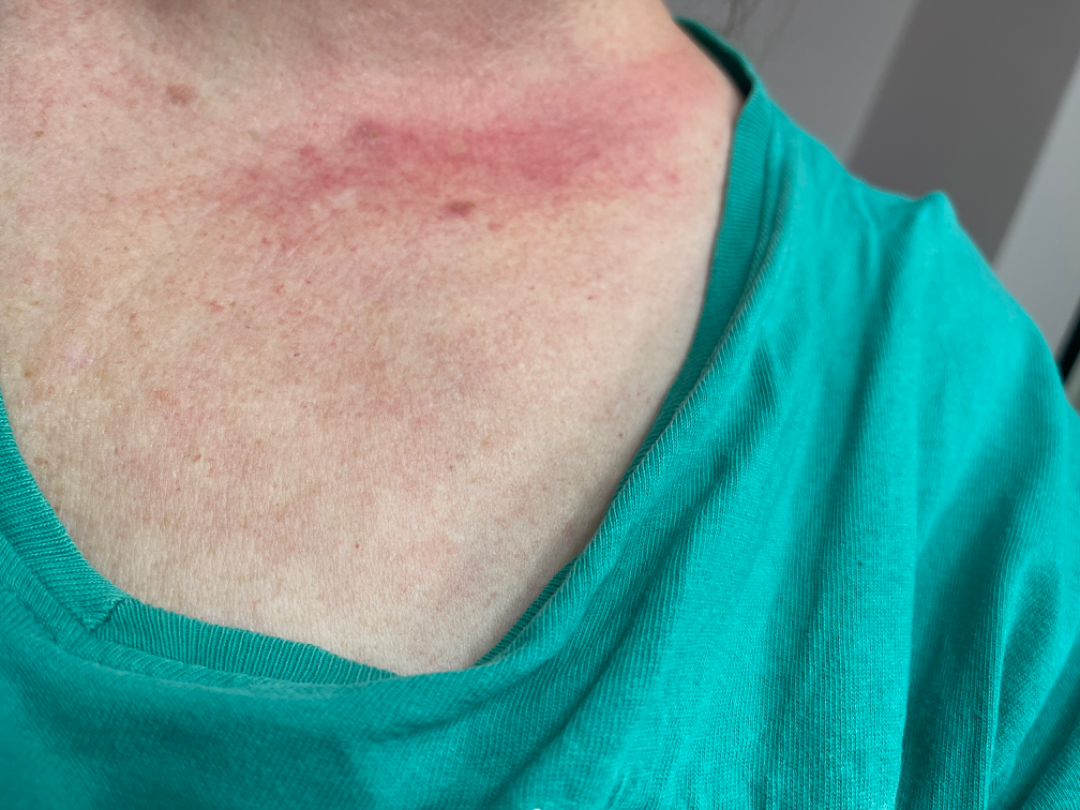Case summary:
– photo taken · at an angle
– described texture · flat
– patient describes the issue as · a rash
– body site · head or neck and front of the torso
– symptom duration · less than one week
– patient-reported symptoms · darkening, burning and itching
– impression · Folliculitis and Eczema were each considered, in no particular order; lower on the differential is Irritant Contact Dermatitis